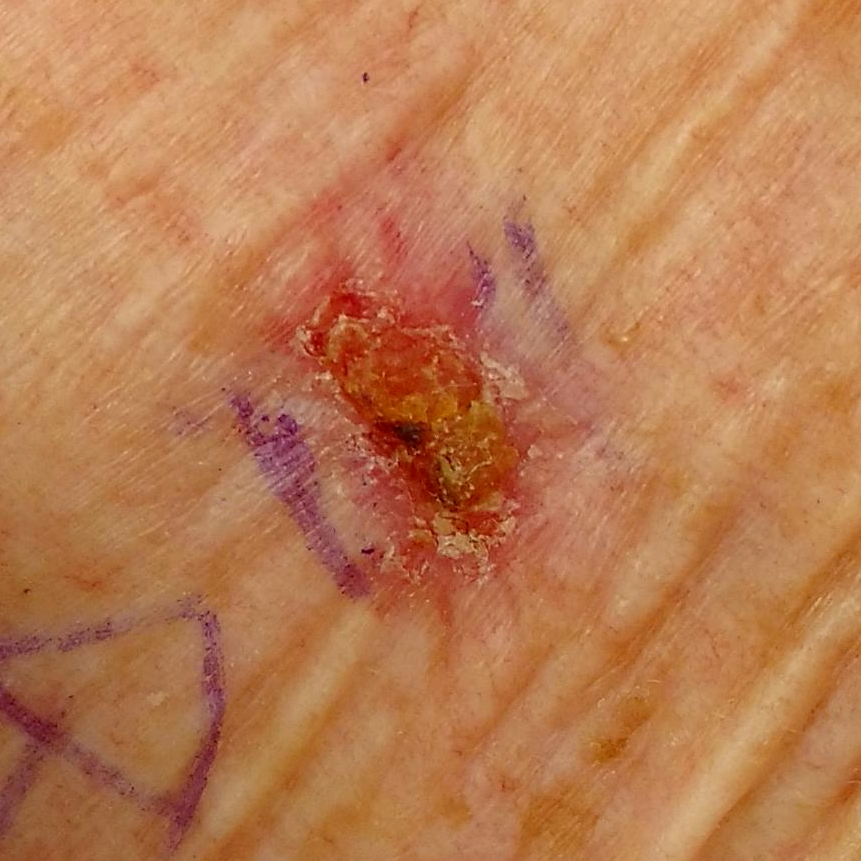Q: How was this image acquired?
A: clinical photograph
Q: Skin phototype?
A: II
Q: Where on the body is the lesion?
A: the chest
Q: Any reported symptoms?
A: pain, elevation, itching, bleeding
Q: What is this lesion?
A: basal cell carcinoma (biopsy-proven)